This is a close-up image:
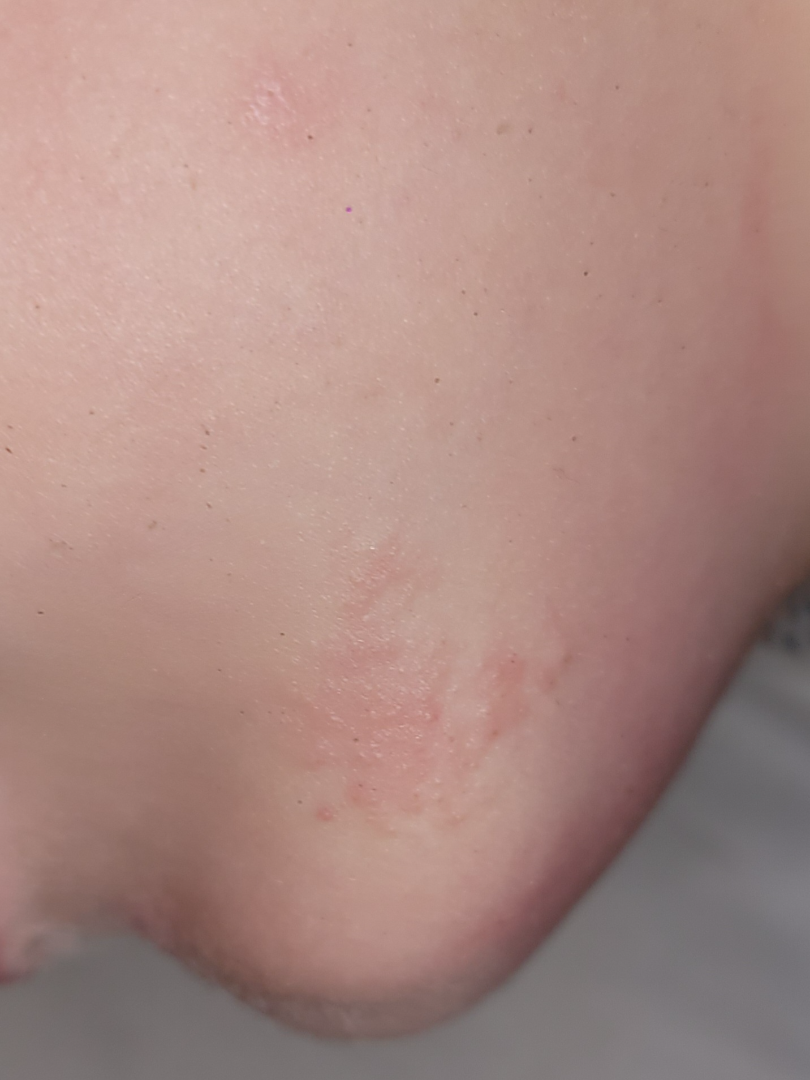assessment: indeterminate